The subject is male; reported duration is about one day; this is a close-up image; the arm is involved; reported lesion symptoms include itching; texture is reported as raised or bumpy; no constitutional symptoms were reported.
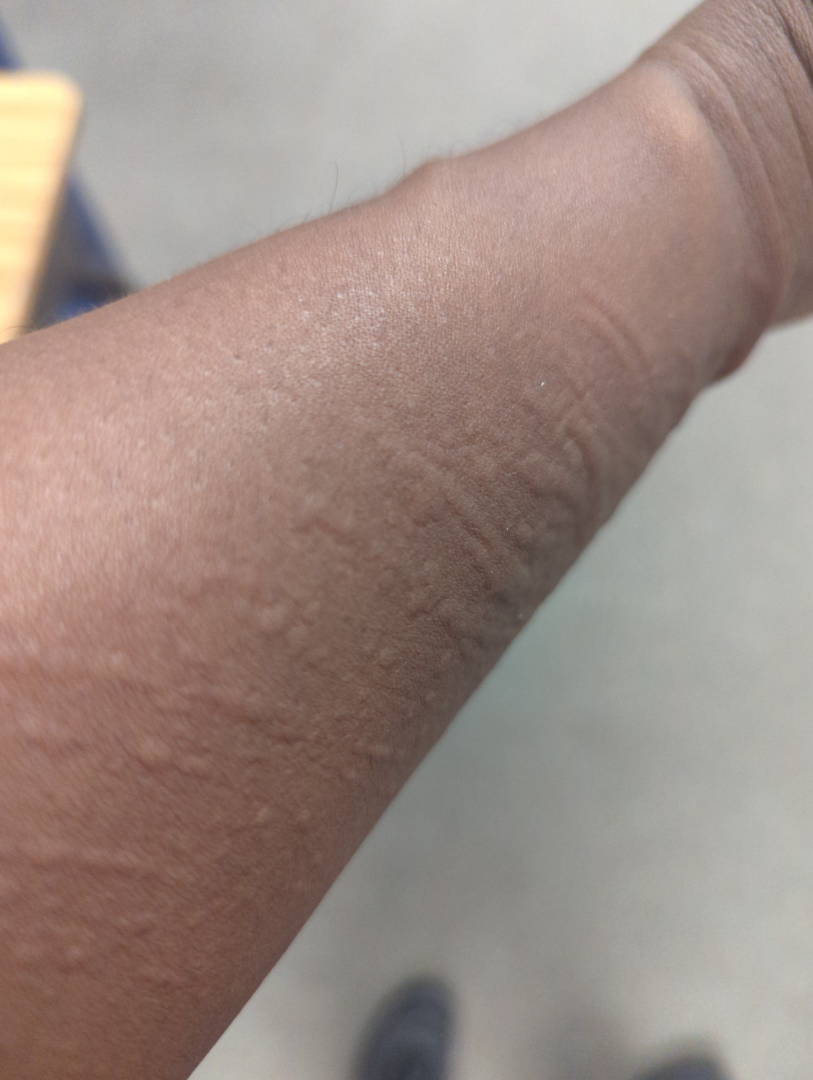impression — three independent reviewers: the leading consideration is Urticaria; lower on the differential is Flagellate erythema; less likely is Leukocytoclastic Vasculitis.